A dermatoscopic image of a skin lesion: 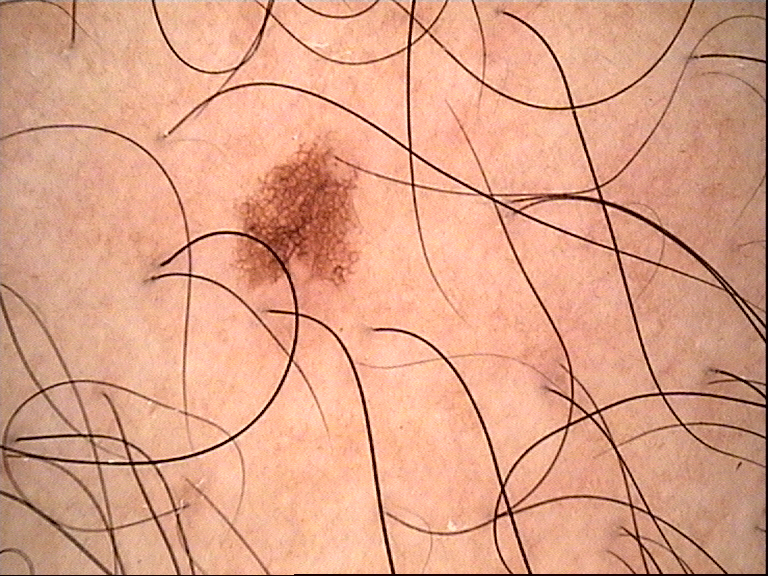Findings: The morphology is that of a banal lesion. Conclusion: Diagnosed as a junctional nevus.